A dermoscopy image of a single skin lesion.
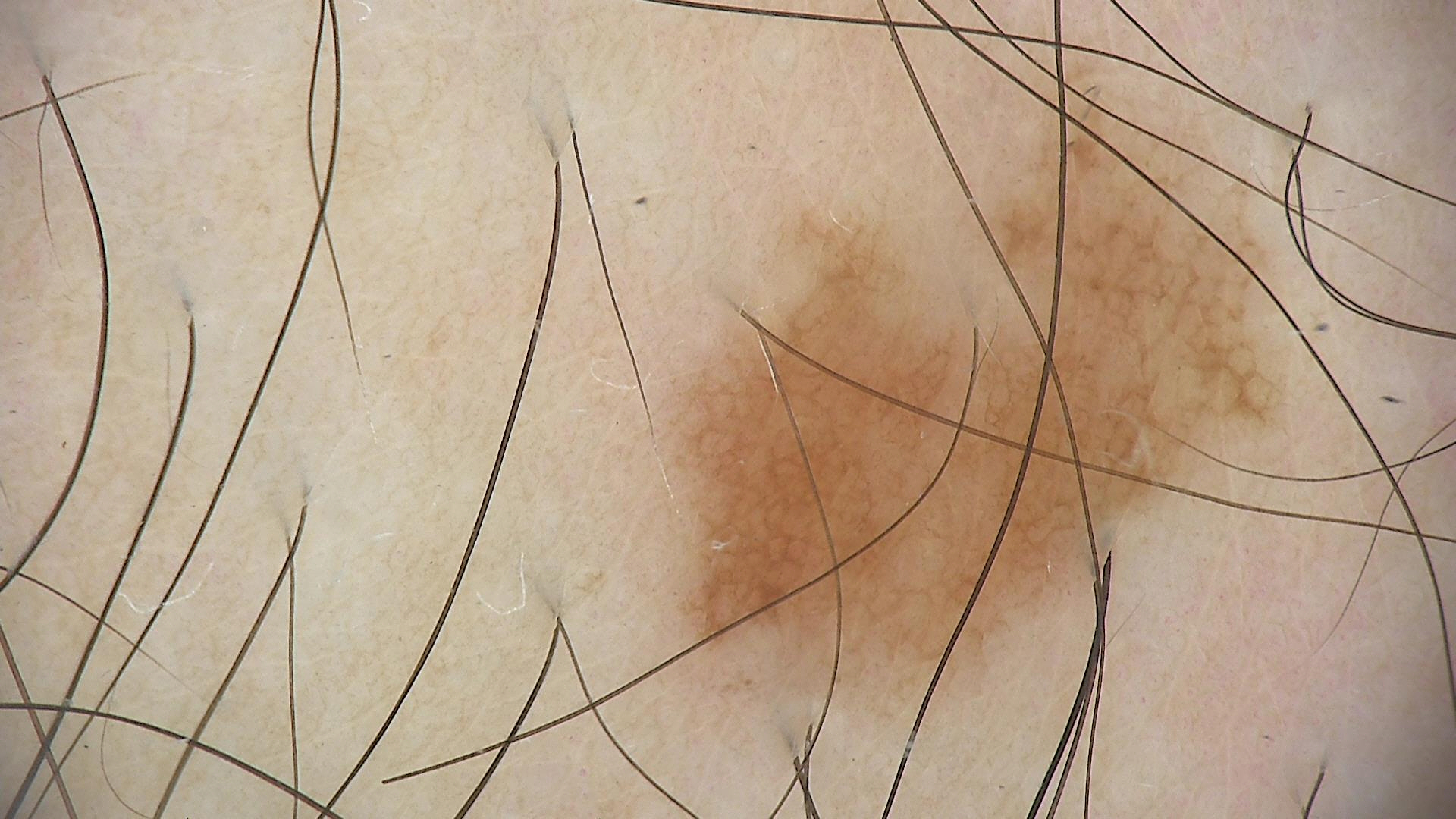Conclusion:
The diagnosis was a benign lesion — a dysplastic junctional nevus.